The leg is involved · the patient considered this a rash · the patient reports the lesion is raised or bumpy · the subject is female · this image was taken at a distance · the patient reports the condition has been present for about one day — 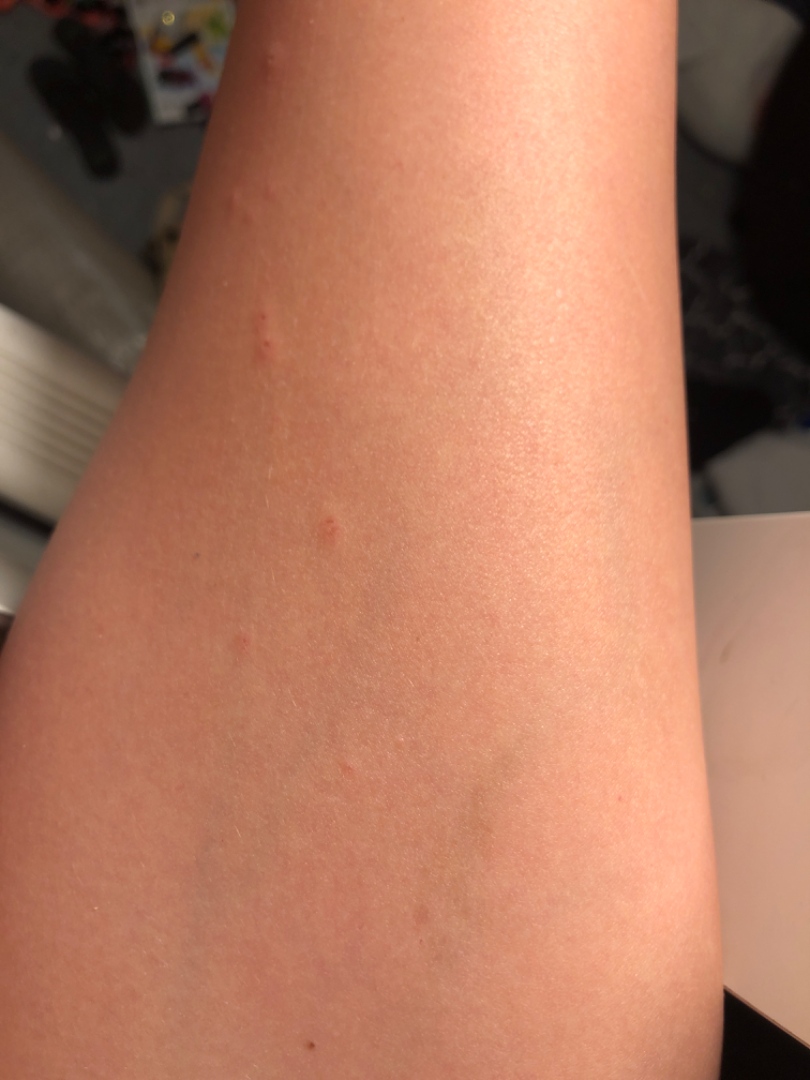assessment = the leading impression is Insect Bite; an alternative is Molluscum Contagiosum; possibly Allergic Contact Dermatitis; lower on the differential is Urticaria.